A dermoscopic photograph of a skin lesion.
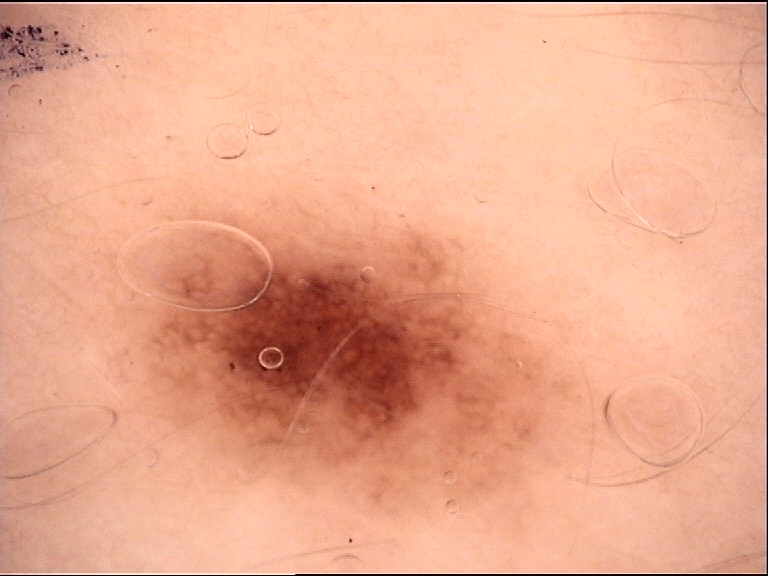label=dysplastic junctional nevus (expert consensus)